A dermoscopic view of a skin lesion: 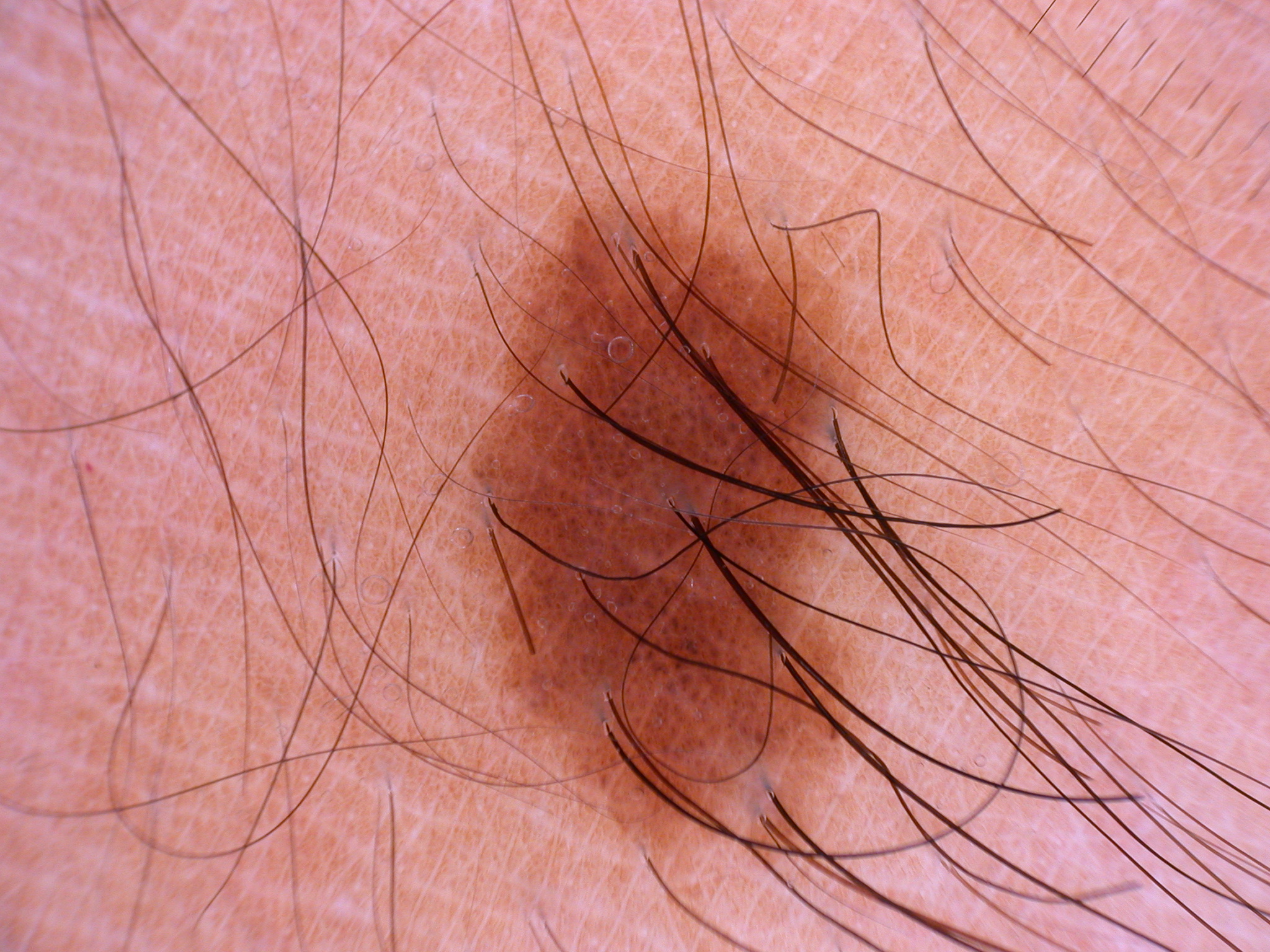Findings:
• location — box(466, 200, 856, 854)
• dermoscopic pattern — globules
• impression — a benign lesion